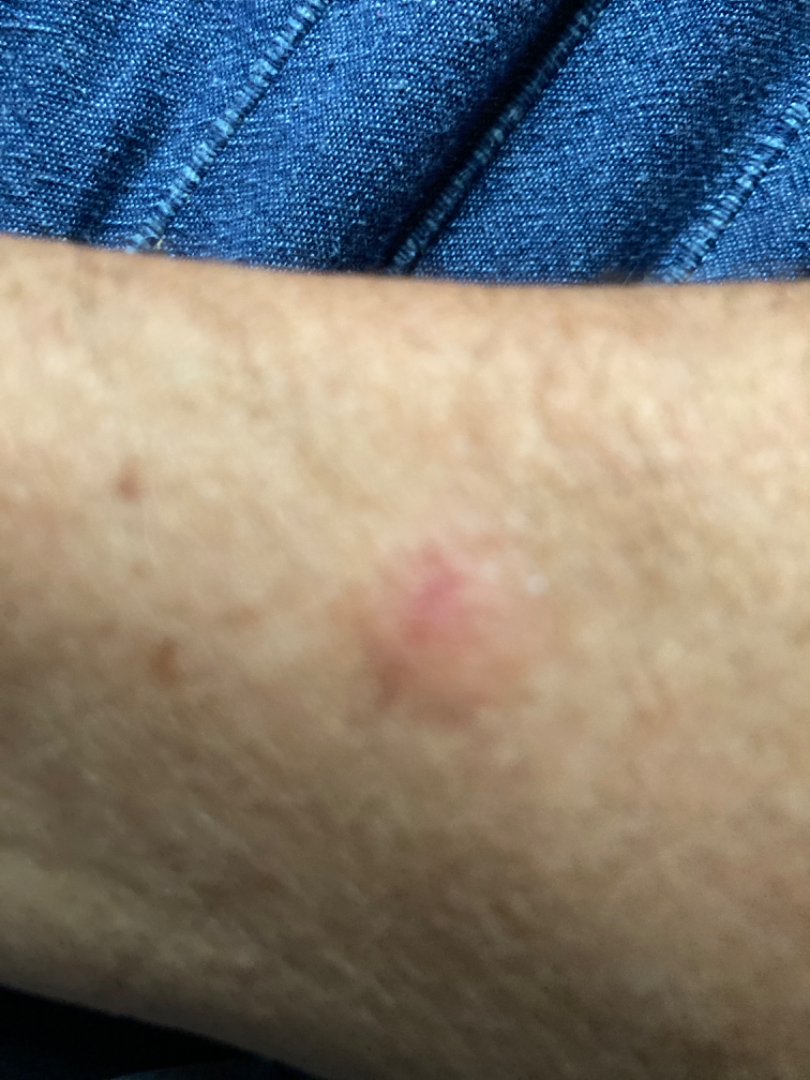Impression:
The skin findings could not be characterized from the image.
History:
Close-up view.